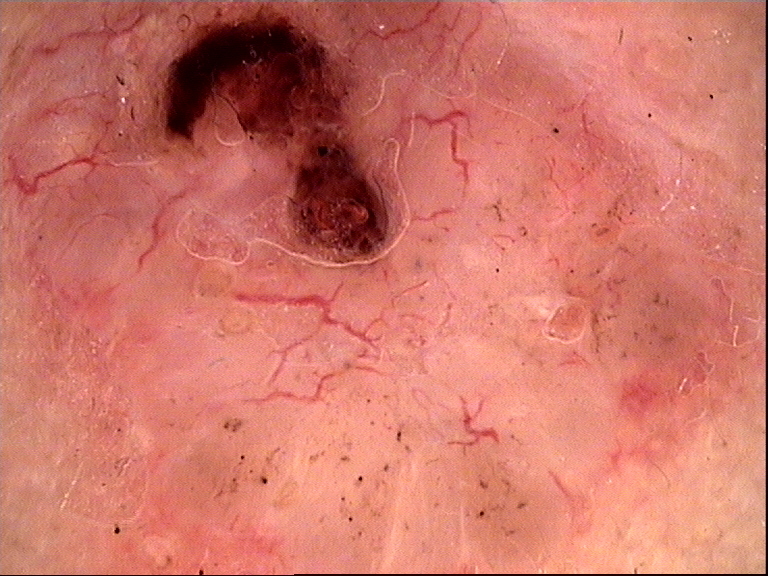diagnosis: basal cell carcinoma (biopsy-proven).